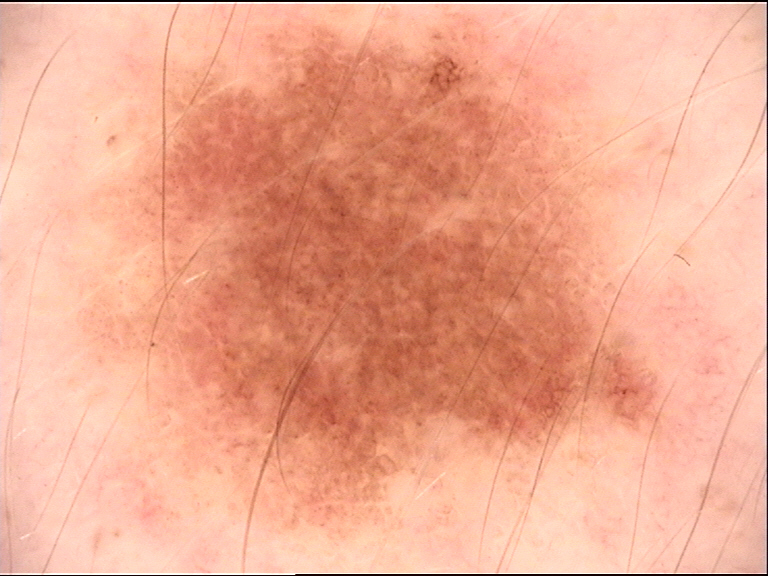{
  "diagnosis": {
    "name": "dysplastic junctional nevus",
    "code": "jd",
    "malignancy": "benign",
    "super_class": "melanocytic",
    "confirmation": "expert consensus"
  }
}